Dermoscopy of a skin lesion.
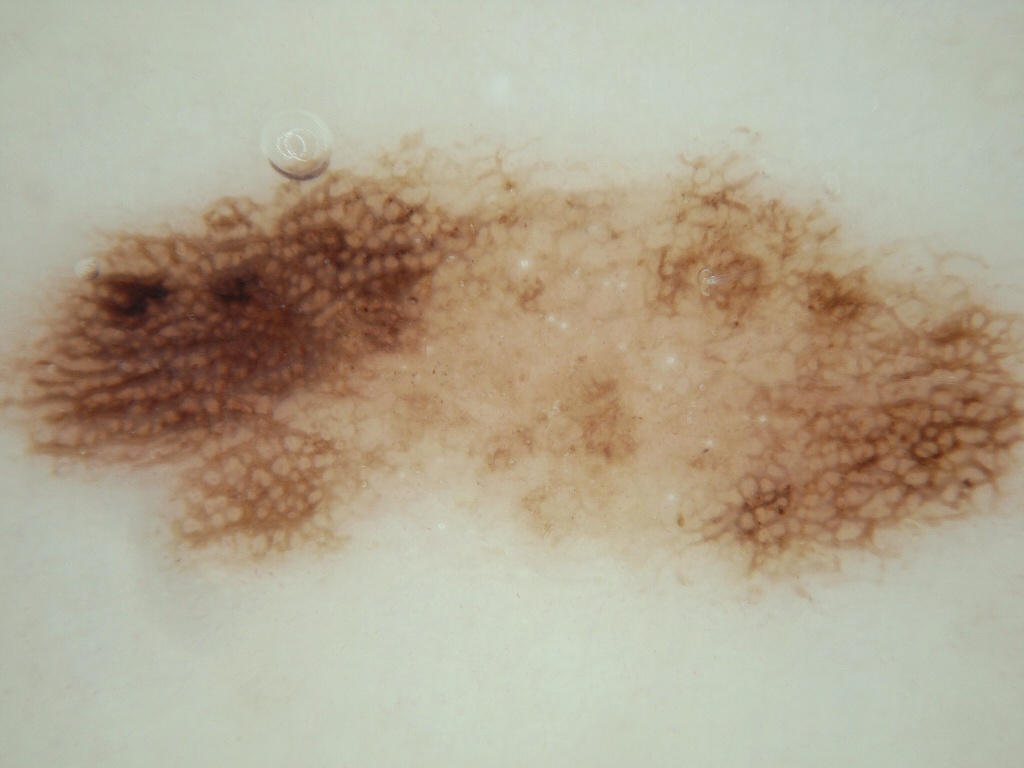On dermoscopy, the lesion shows pigment network and milia-like cysts, with no streaks, negative network, or globules.
In (x1, y1, x2, y2) order, the lesion's extent is box(2, 110, 1017, 624).
Consistent with a melanocytic nevus, a benign skin lesion.